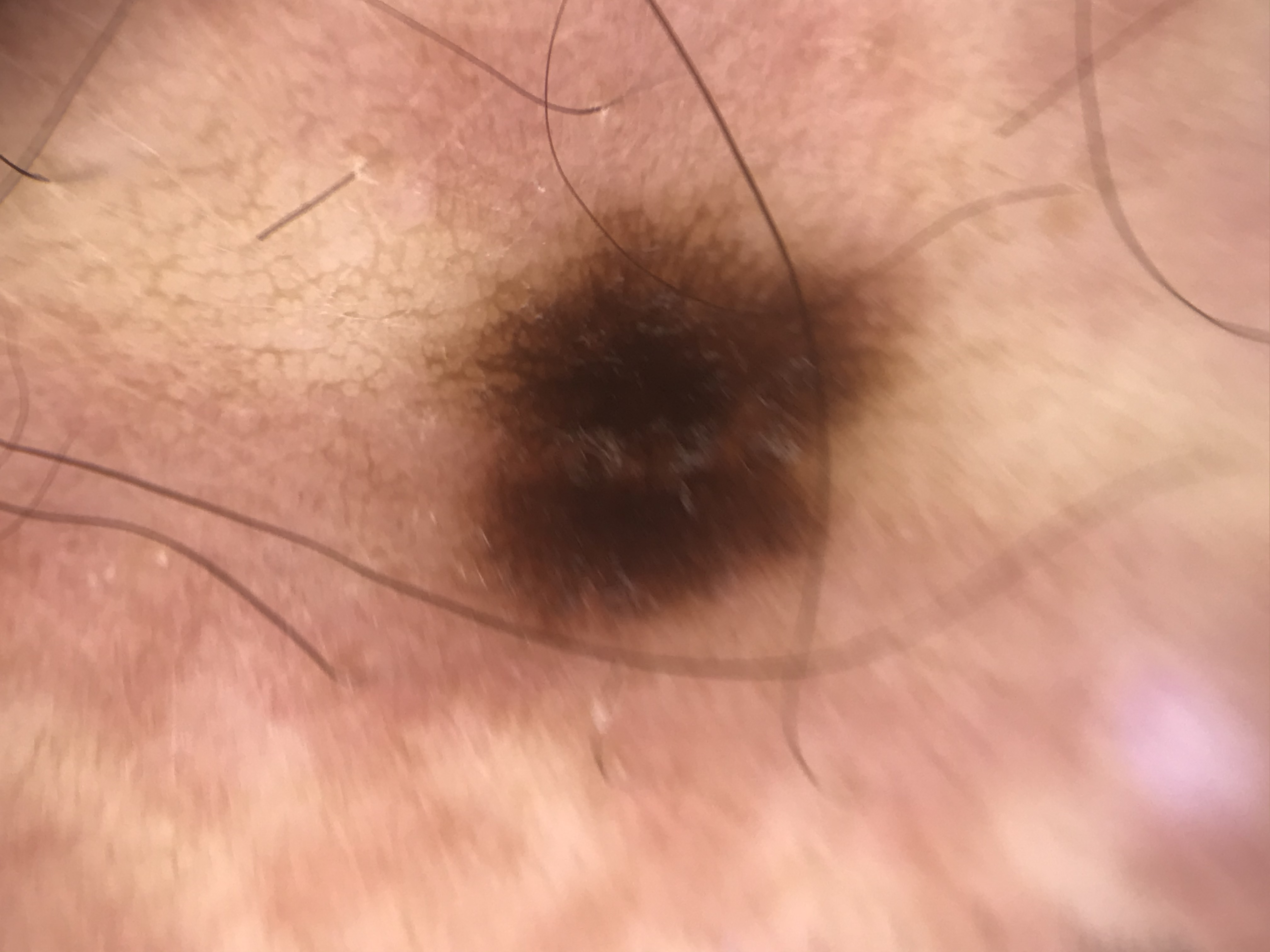diagnosis: junctional nevus (expert consensus)